A smartphone photograph of a skin lesion. A female patient in their early 30s. The patient was assessed as skin type III. History notes prior malignancy (patient or family) and prior skin cancer (patient or family).
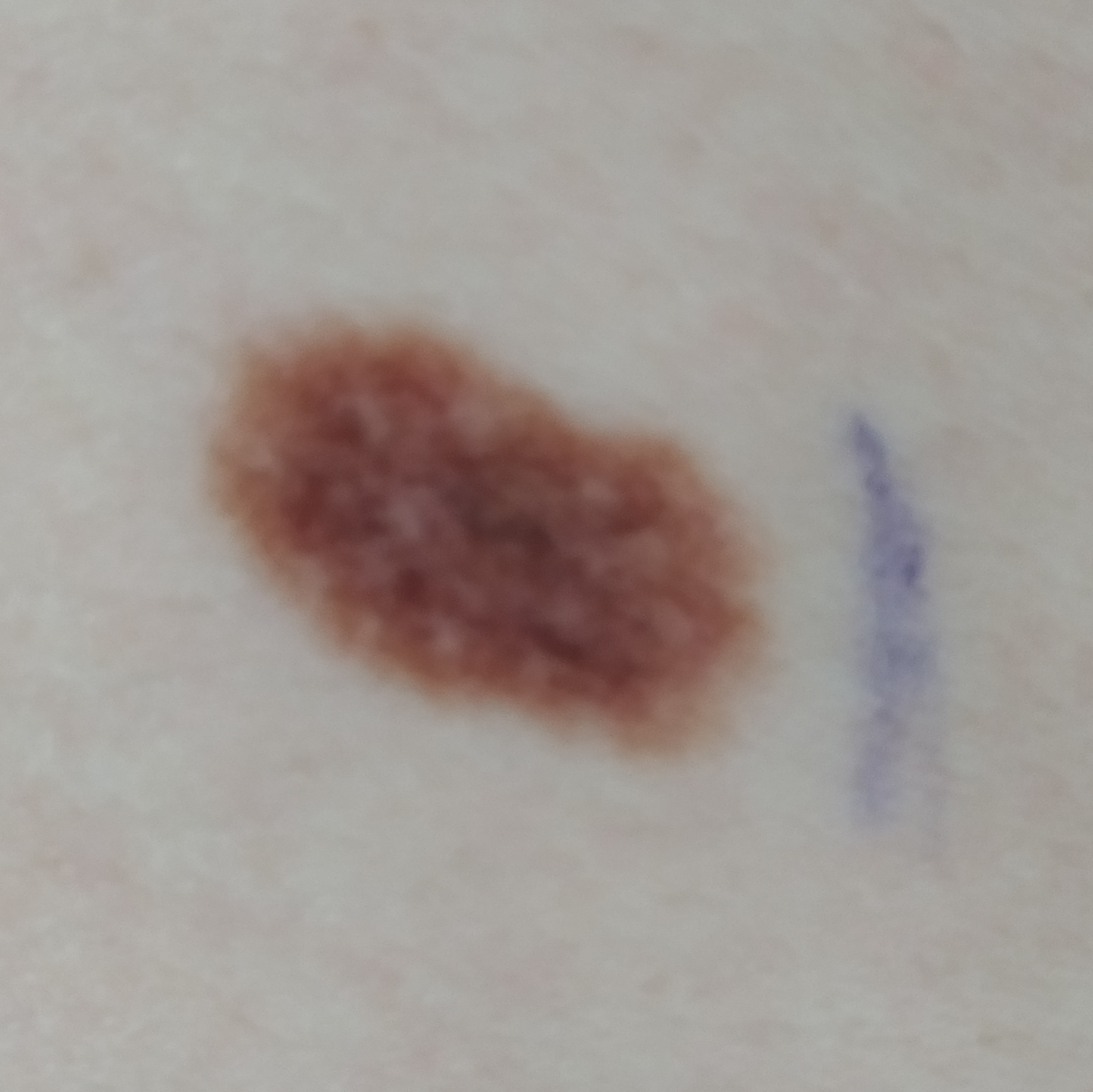Patient and lesion:
Located on the back. The lesion measures approximately 15 × 8 mm. The patient reports that the lesion does not itch and does not hurt.
Conclusion:
On biopsy, the diagnosis was a benign skin lesion — a nevus.